A dermoscopy image of a single skin lesion: 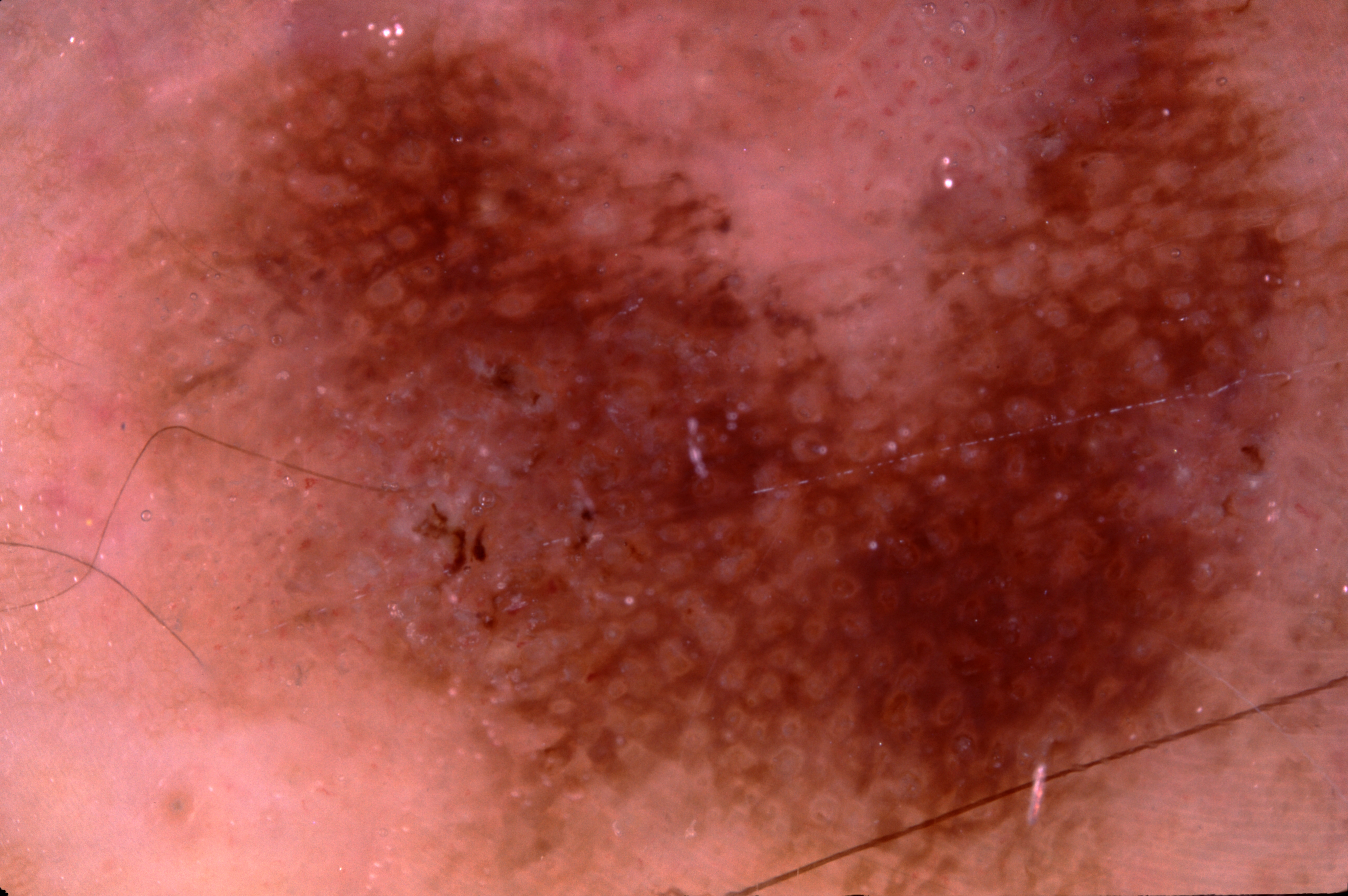features = pigment network; absent: milia-like cysts, negative network, and streaks
lesion extent = spans the dermoscopic field
diagnosis = a seborrheic keratosis, a benign lesion